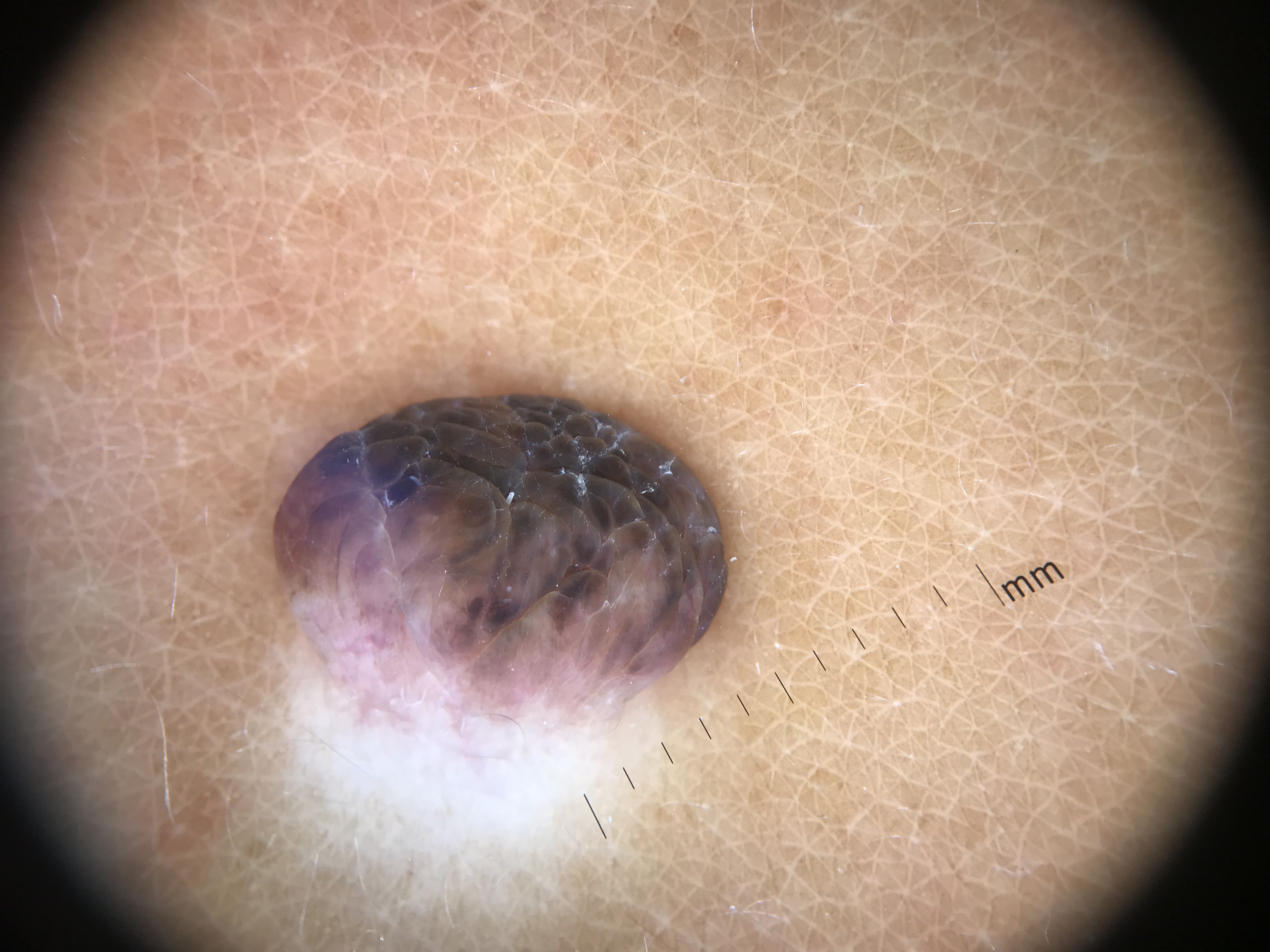Findings: A dermatoscopic image of a skin lesion. This is a banal lesion. Impression: Labeled as a dermal nevus.